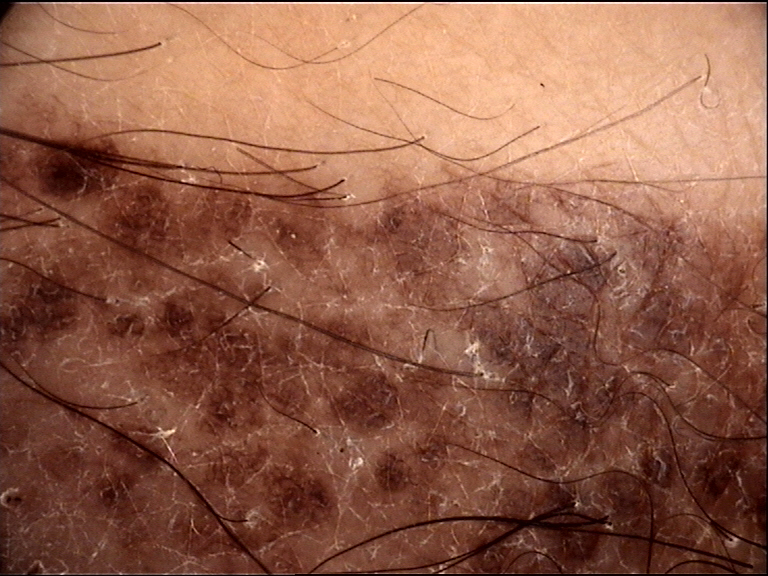A dermoscopic photograph of a skin lesion.
Classified as a banal lesion — a congenital compound nevus.